An image taken at an angle.
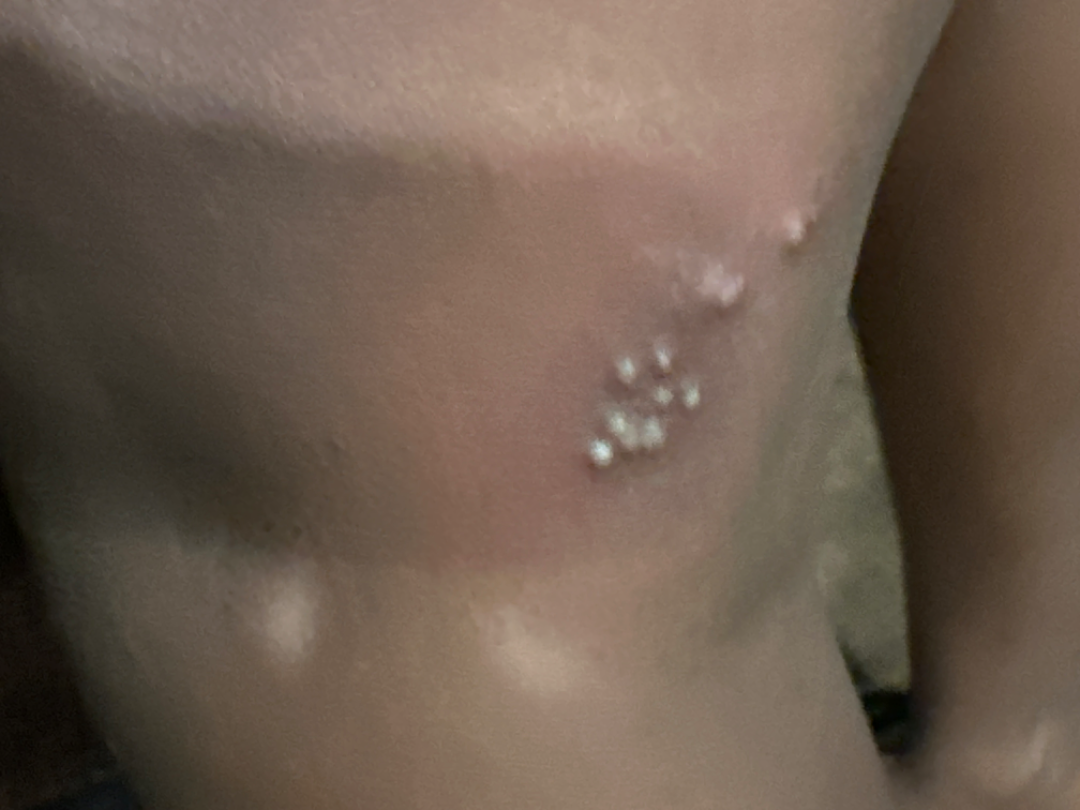Impression:
Consistent with Milia.